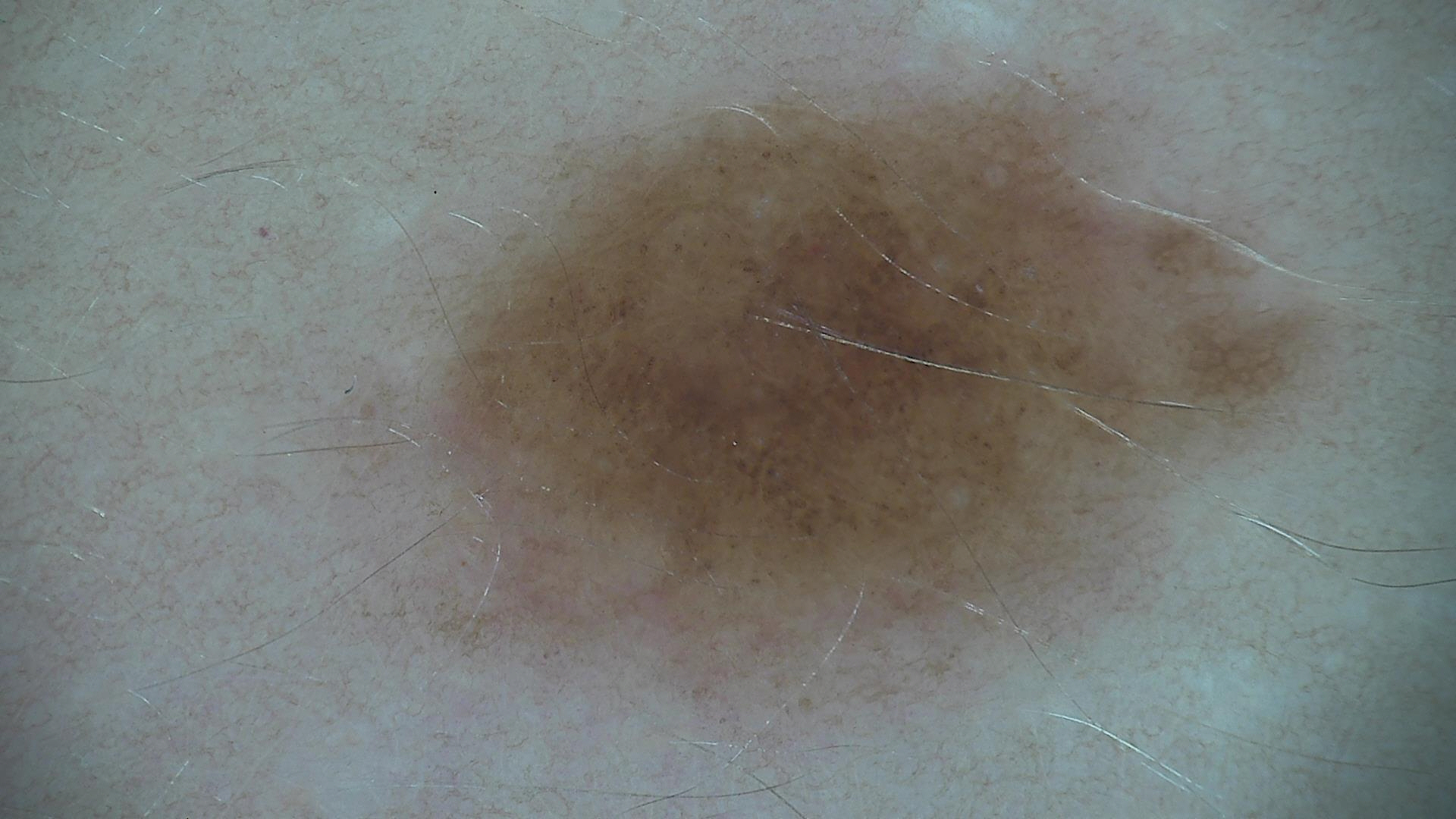Q: What was the diagnostic impression?
A: dysplastic junctional nevus (expert consensus)